A dermoscopic photograph of a skin lesion.
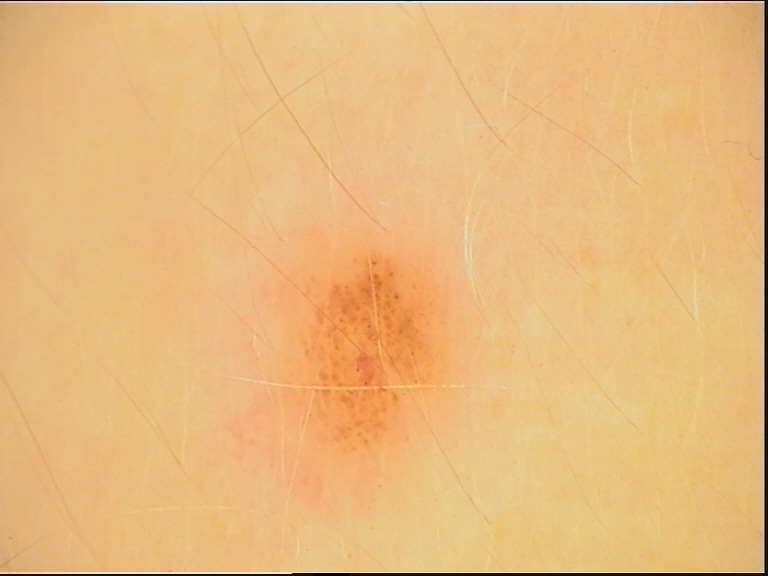Findings:
– class — junctional nevus (expert consensus)